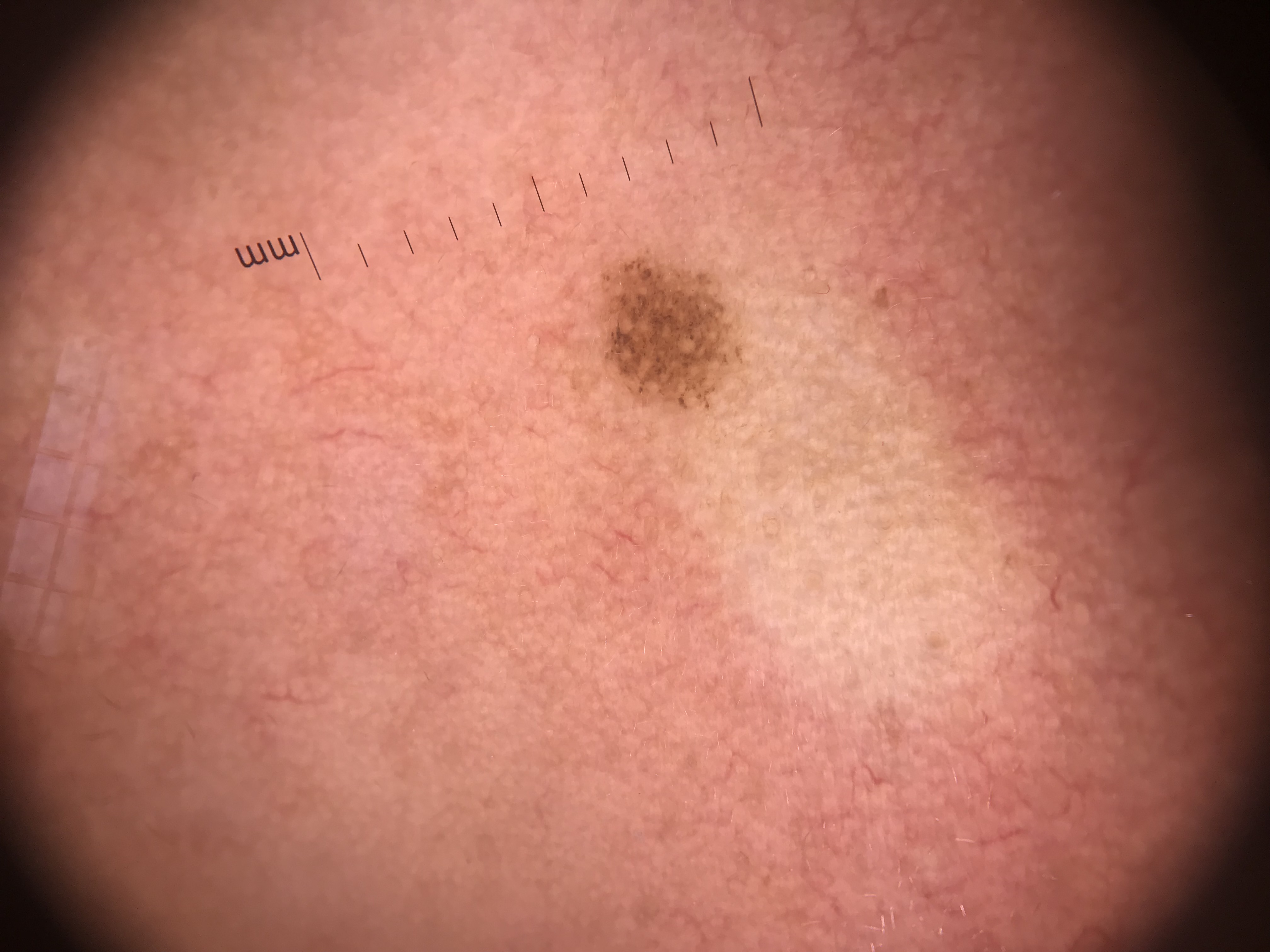image: dermatoscopy
diagnosis:
  name: Miescher nevus
  code: mcb
  malignancy: benign
  super_class: melanocytic
  confirmation: expert consensus